The patient reports itching, the patient considered this a rash, the photo was captured at an angle, the affected area is the leg, the subject is a male aged 30–39 — 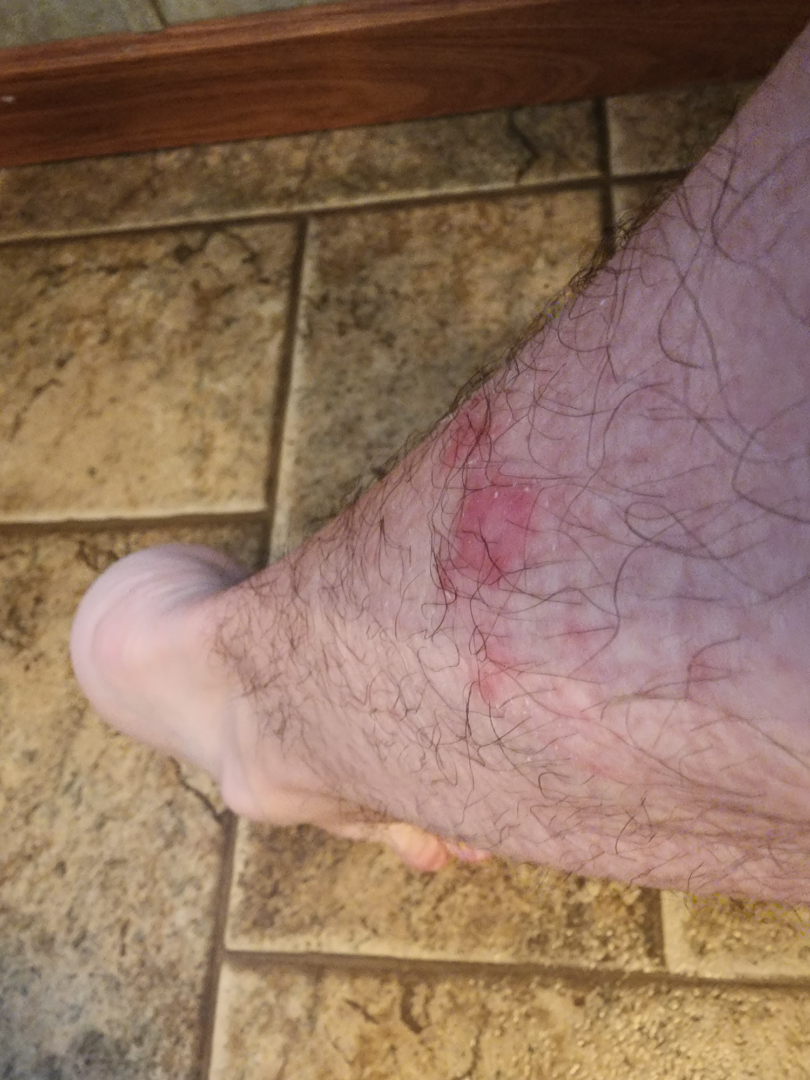Findings:
Allergic Contact Dermatitis and Irritant Contact Dermatitis were each considered, in no particular order.